A female patient aged around 65. Recorded as FST I. A skin lesion imaged with contact-polarized dermoscopy. The chart notes a previous melanoma.
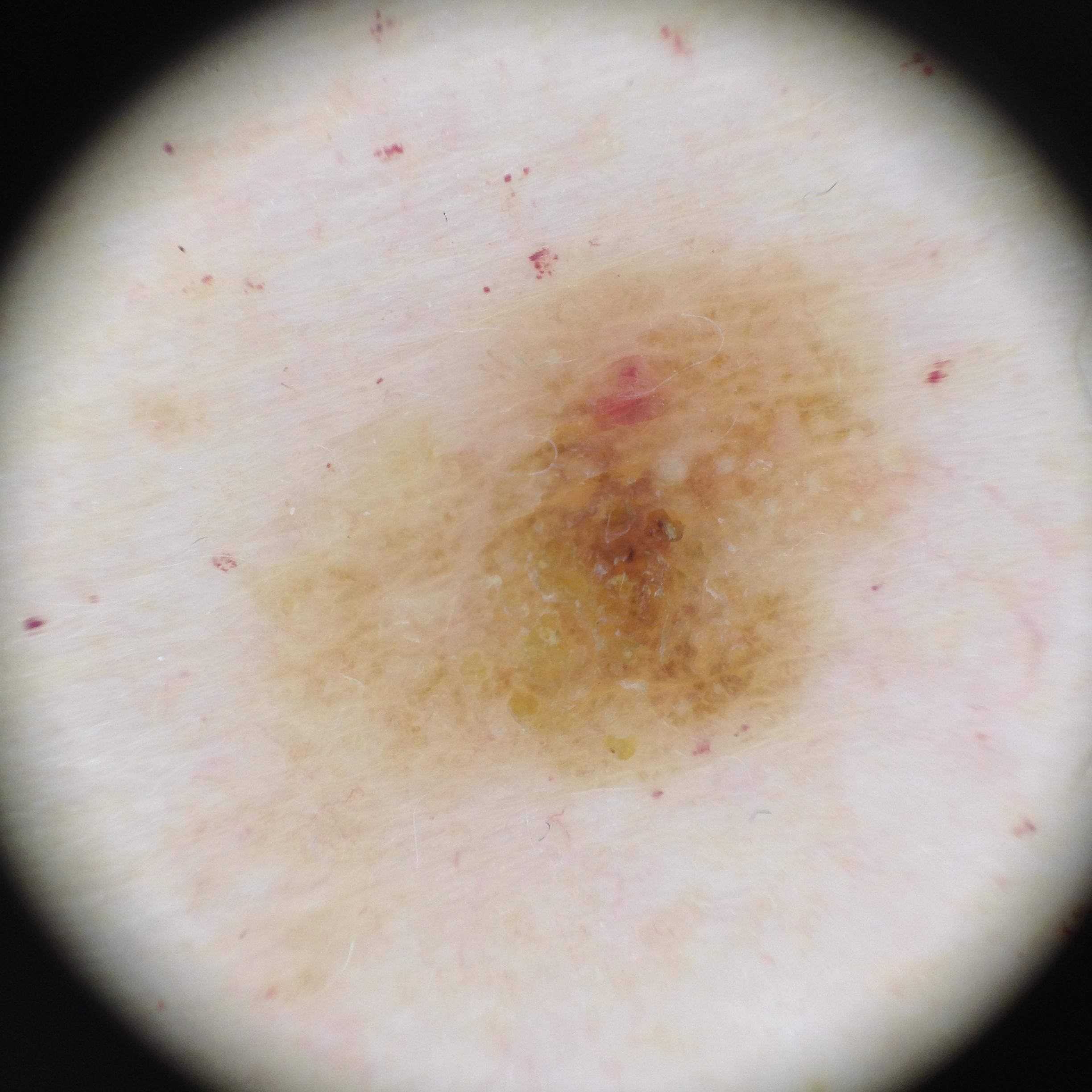  lesion_location:
    region: the trunk
    detail: the anterior trunk
  diagnosis:
    name: Seborrheic keratosis
    malignancy: benign
    confirmation: expert clinical impression
    lineage: epidermal